The patient reports a personal history of cancer; the patient says their skin tans without first burning; imaged for a research study, with no referral diagnosis recorded; a female patient 84 years of age; dermoscopy of a skin lesion; the patient describes having few moles overall — 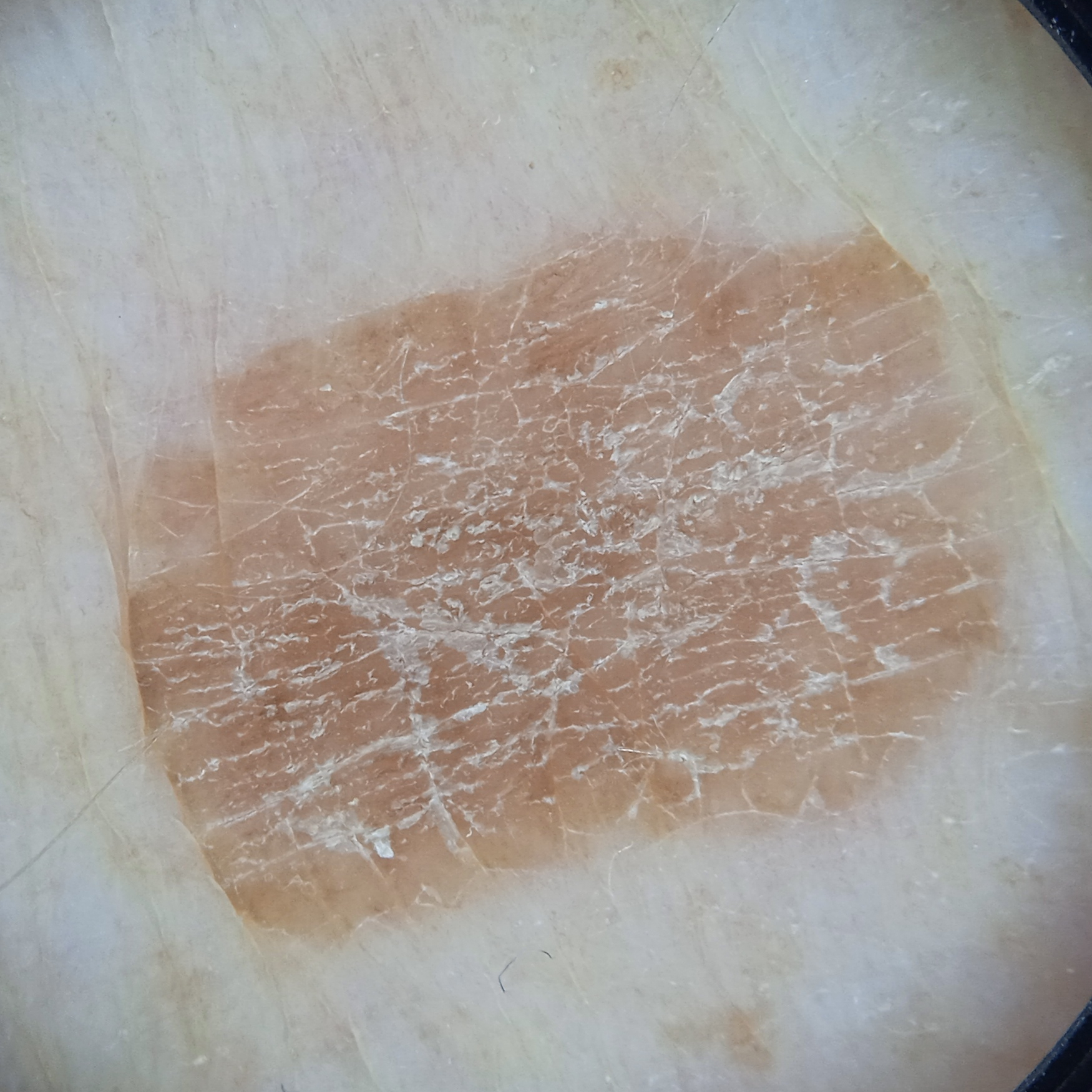The lesion is on an arm.
Measuring roughly 11.2 mm.
The diagnostic impression was a seborrheic keratosis.